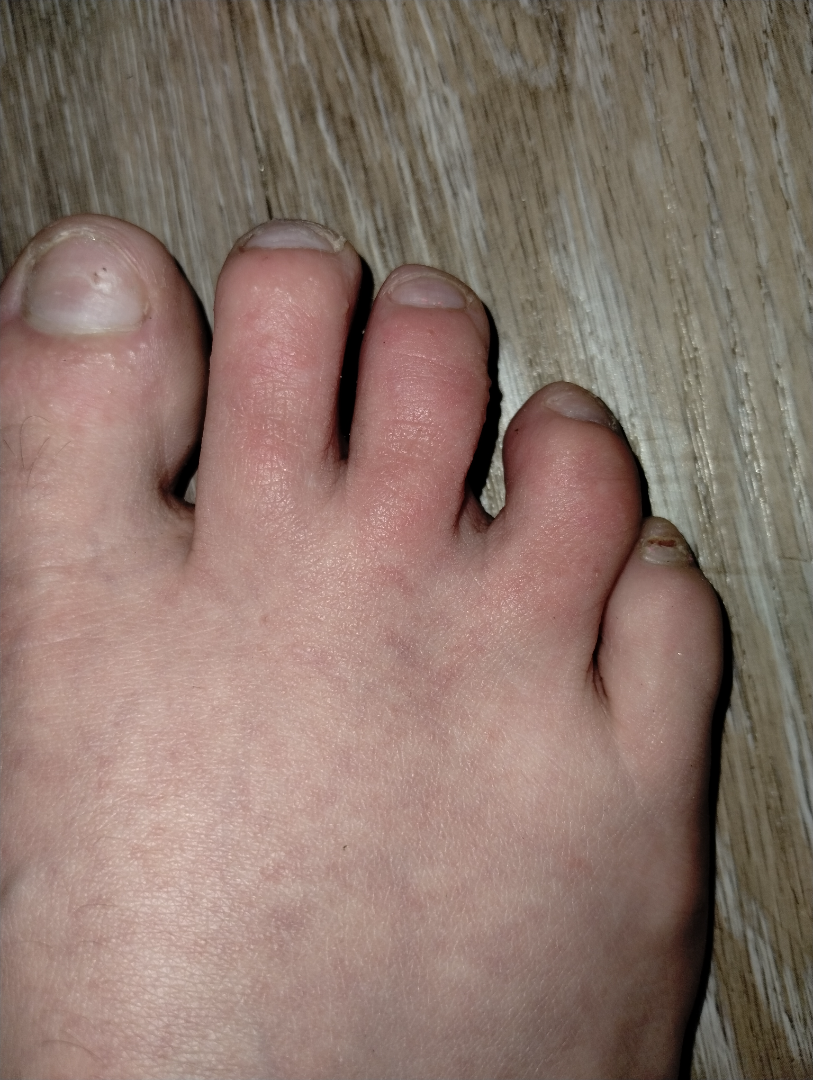<report>
  <assessment>no clear pathology</assessment>
  <skin_tone>
    <fitzpatrick>II</fitzpatrick>
    <monk_skin_tone>1, 2</monk_skin_tone>
  </skin_tone>
  <shot_type>close-up</shot_type>
</report>